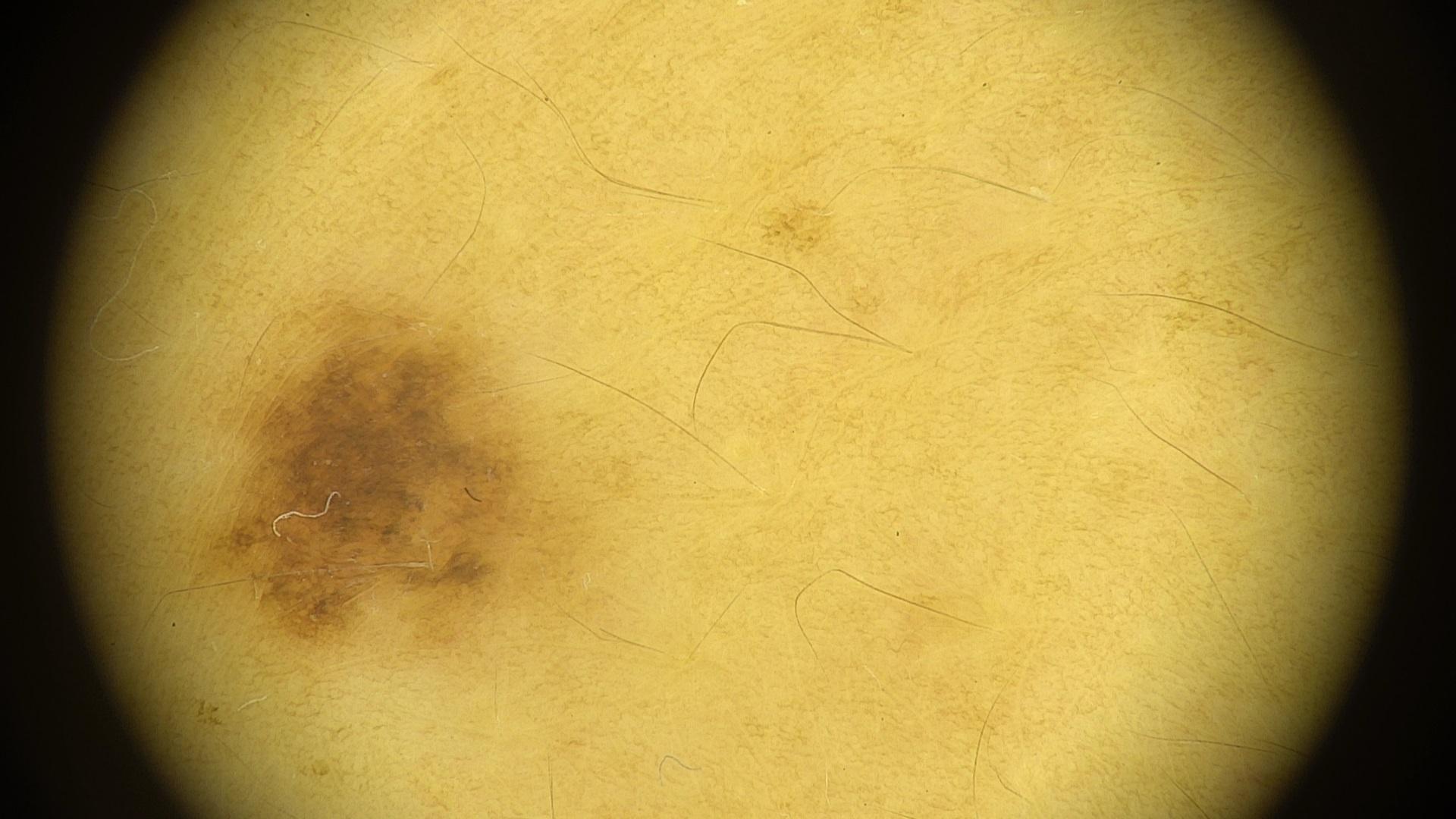Findings:
– assessment: Nevus